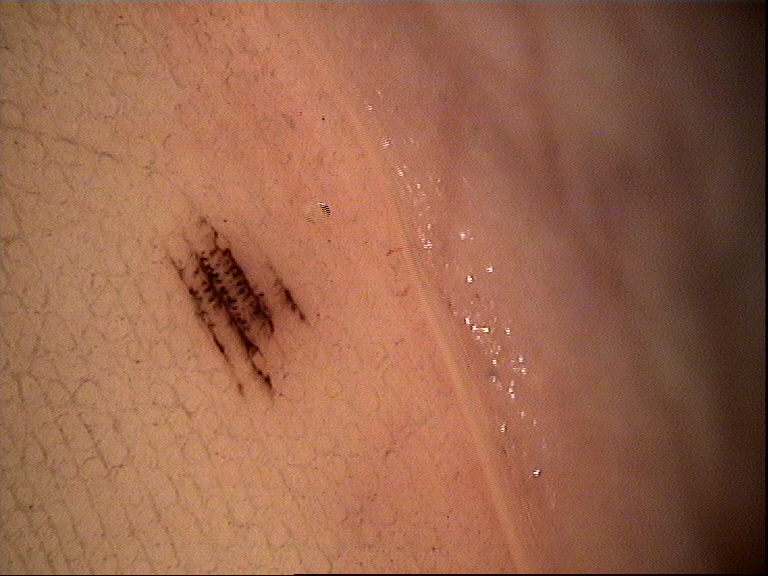image type: dermatoscopy | diagnosis: acral dysplastic junctional nevus (expert consensus).